A skin lesion imaged with a dermatoscope.
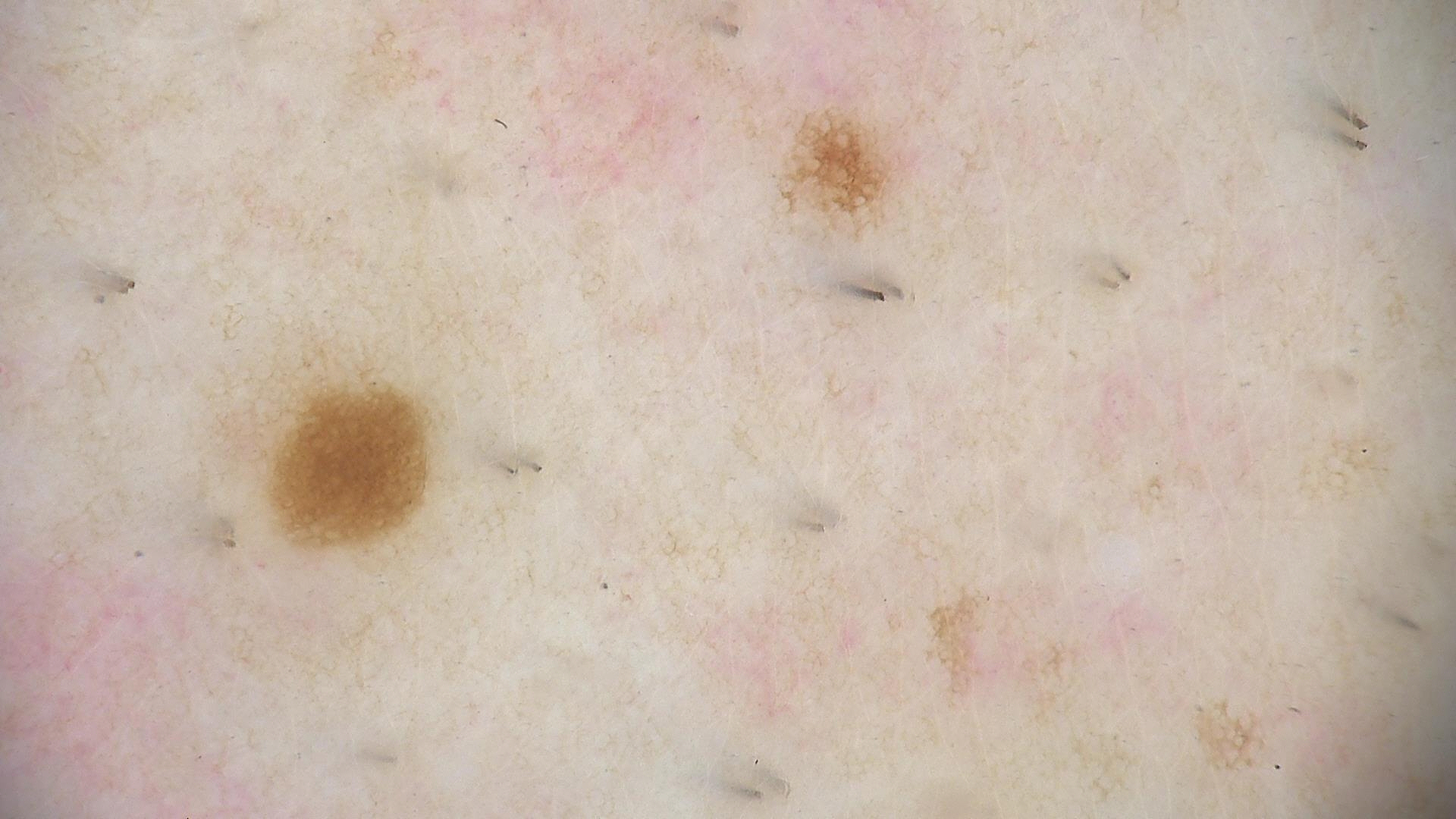label — dysplastic junctional nevus (expert consensus).